Dermoscopy of a skin lesion.
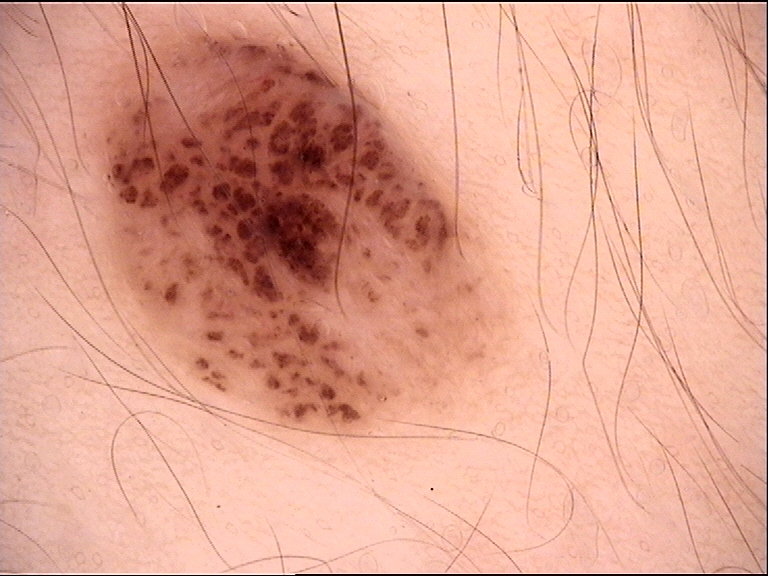{
  "diagnosis": {
    "name": "dermal nevus",
    "code": "db",
    "malignancy": "benign",
    "super_class": "melanocytic",
    "confirmation": "expert consensus"
  }
}